A dermoscopic photograph of a skin lesion: 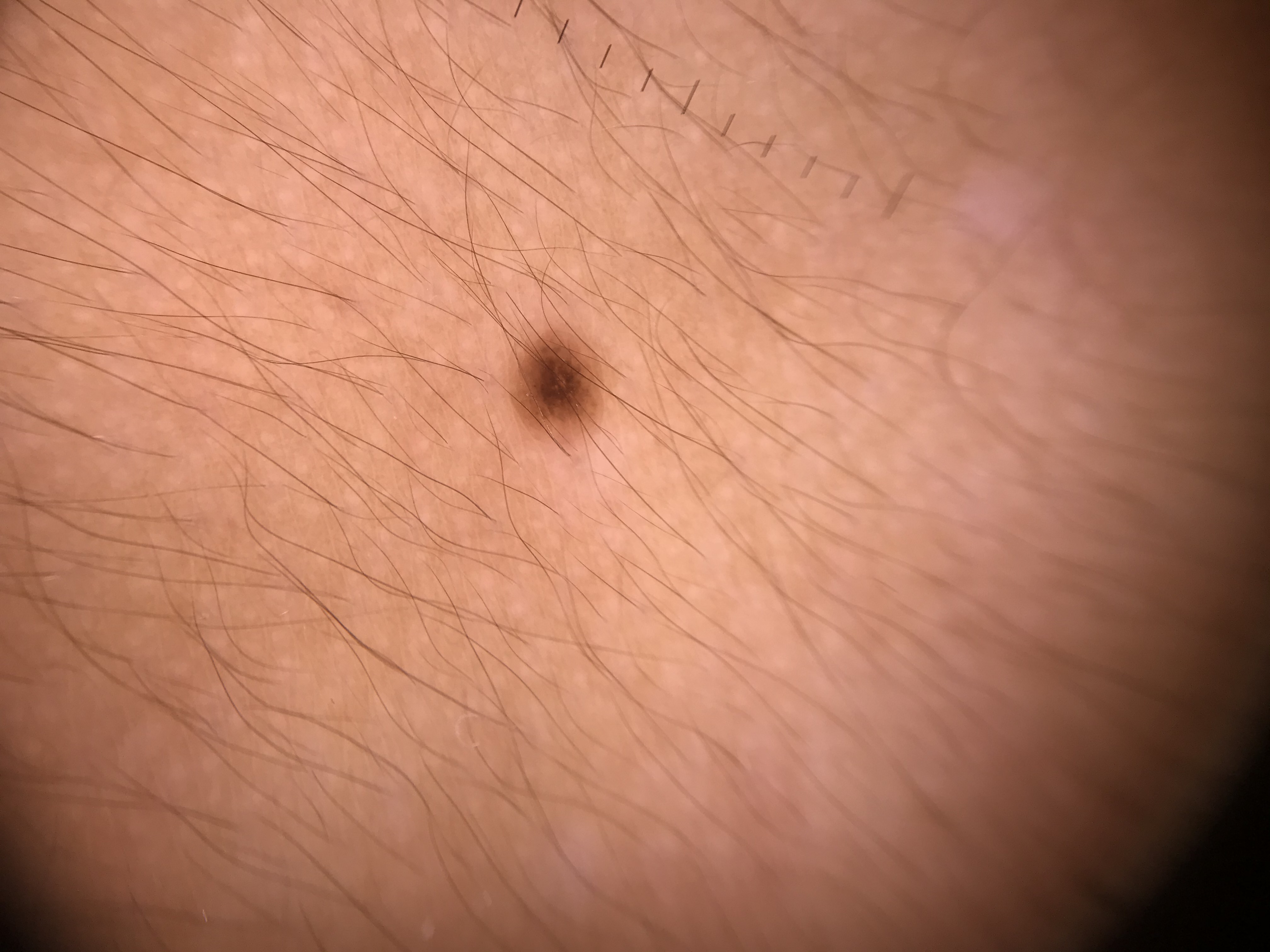| feature | finding |
|---|---|
| lesion type | banal |
| diagnostic label | junctional nevus (expert consensus) |